This image was taken at an angle. The lesion involves the arm and palm: 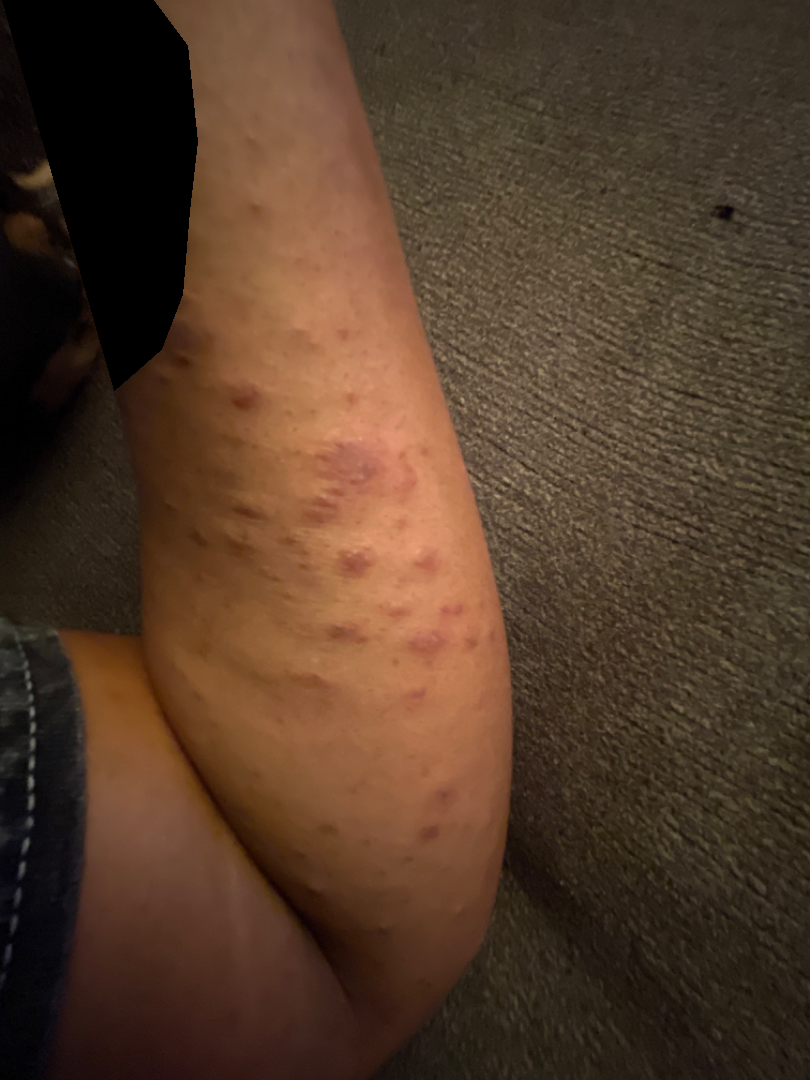diagnostic considerations = most consistent with Pityriasis lichenoides; also raised was Psoriasis.